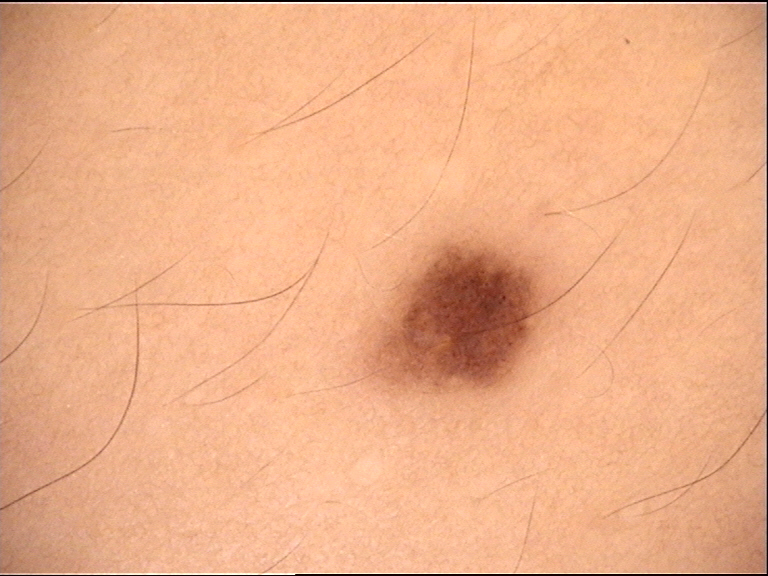A dermatoscopic image of a skin lesion. Labeled as a banal lesion — a junctional nevus.